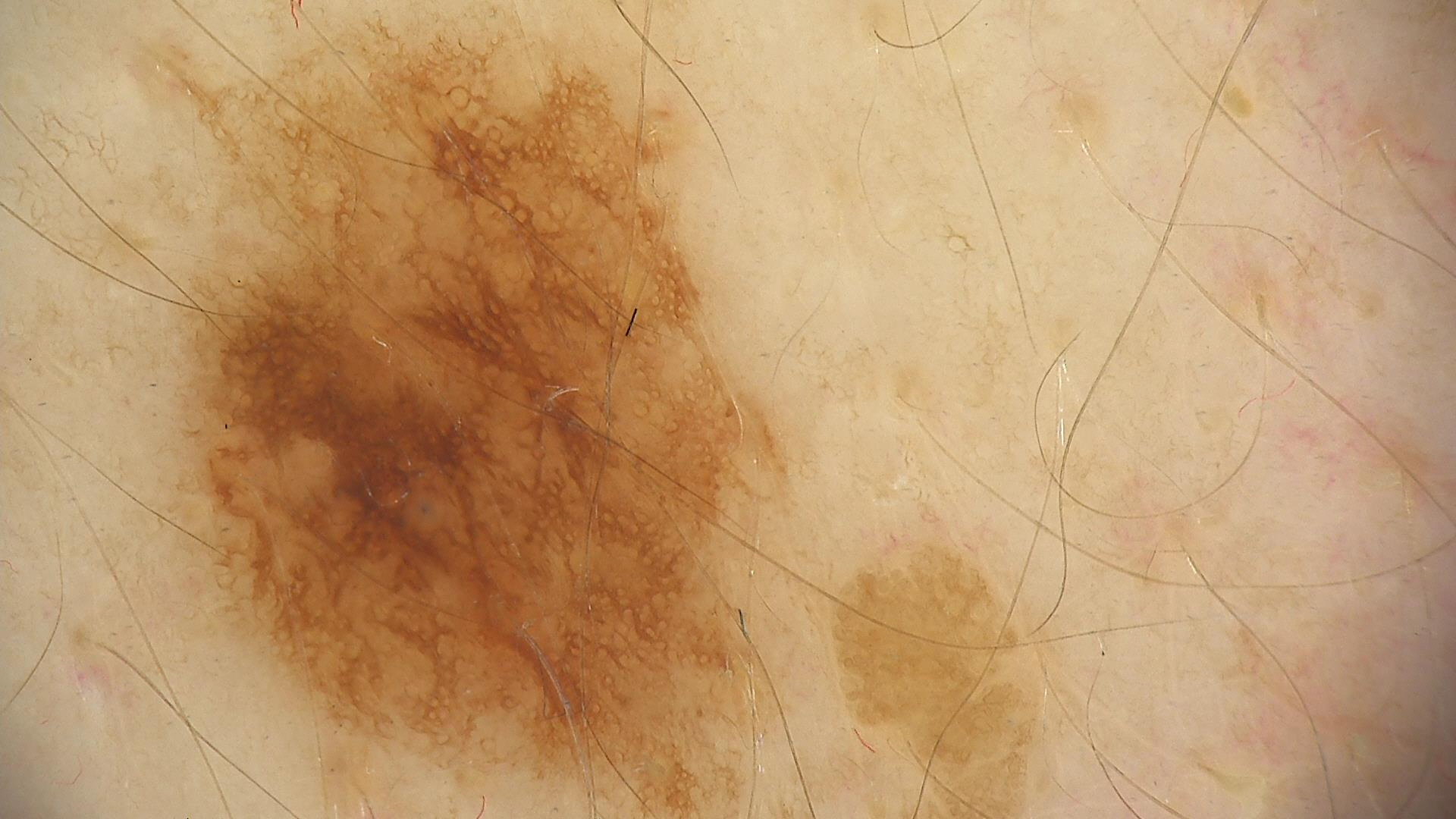The diagnostic label was a dysplastic junctional nevus.